Dermoscopy of a skin lesion:
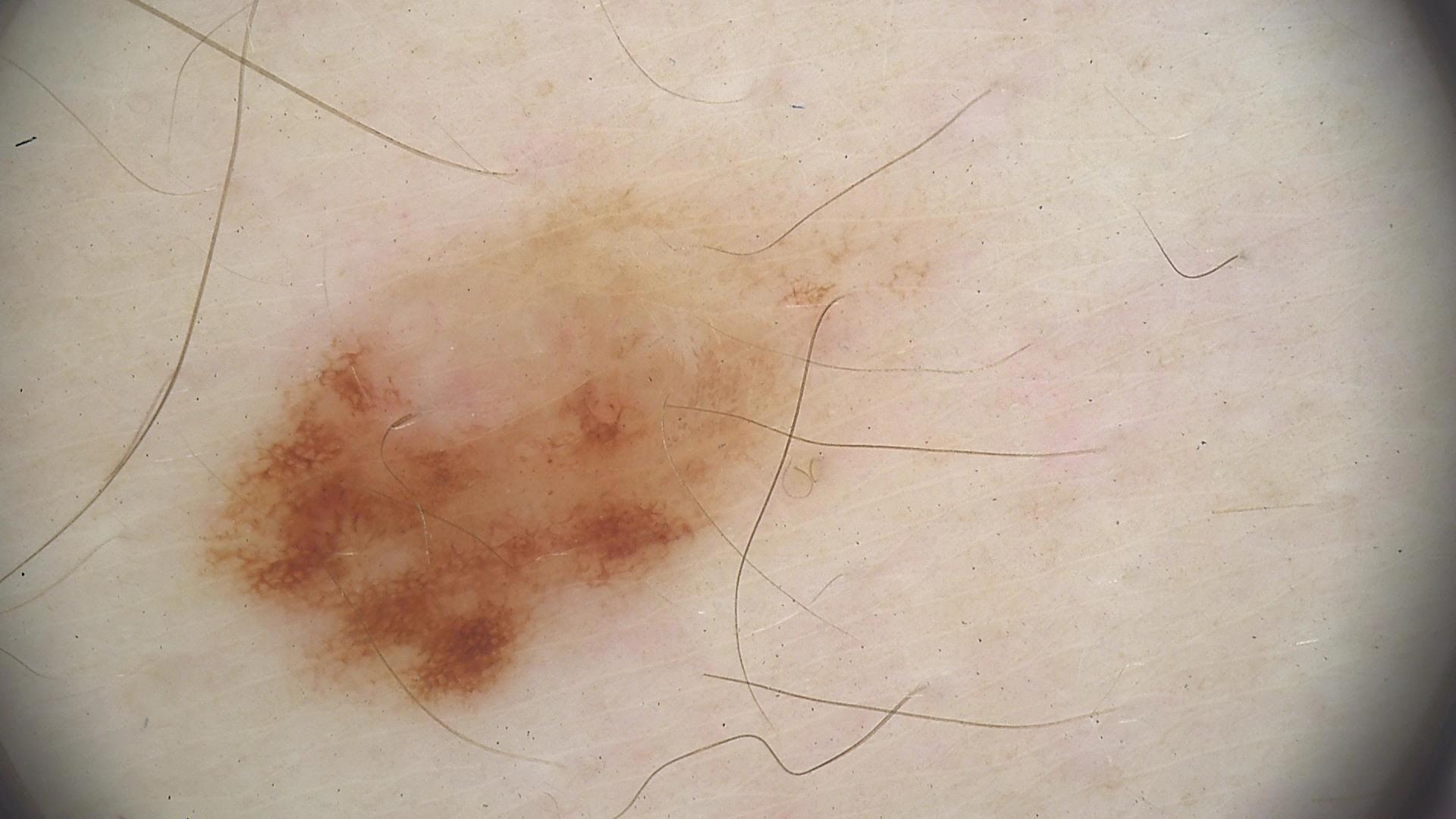class = dysplastic junctional nevus (expert consensus).